A skin lesion imaged with a dermatoscope.
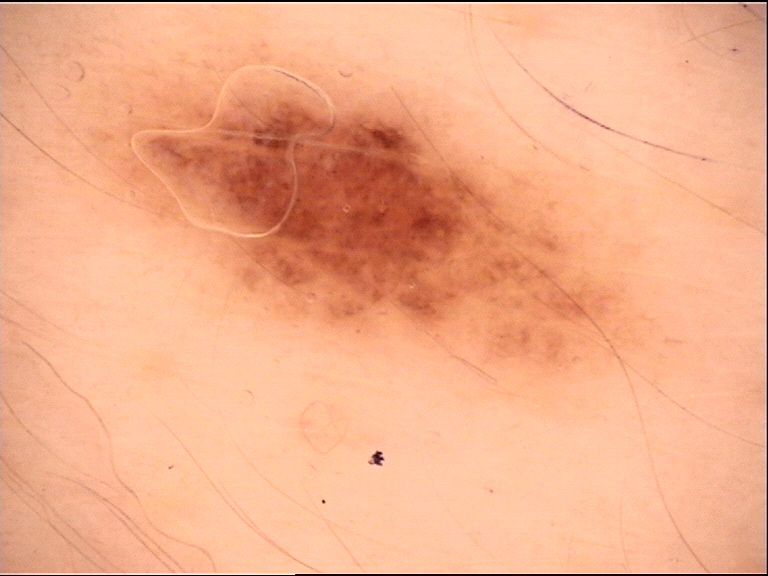Impression:
The diagnostic label was a benign lesion — a dysplastic junctional nevus.